The top or side of the foot, leg and front of the torso are involved; female contributor, age 18–29; the photograph was taken at an angle: 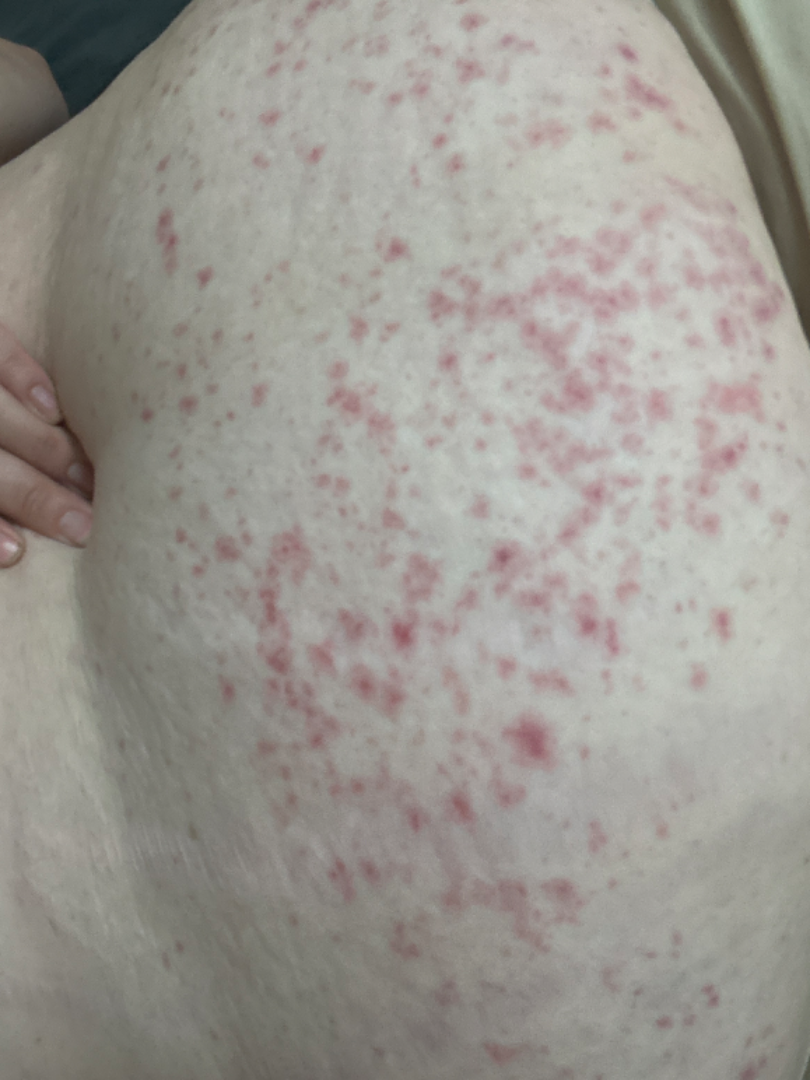Findings:
* assessment · indeterminate